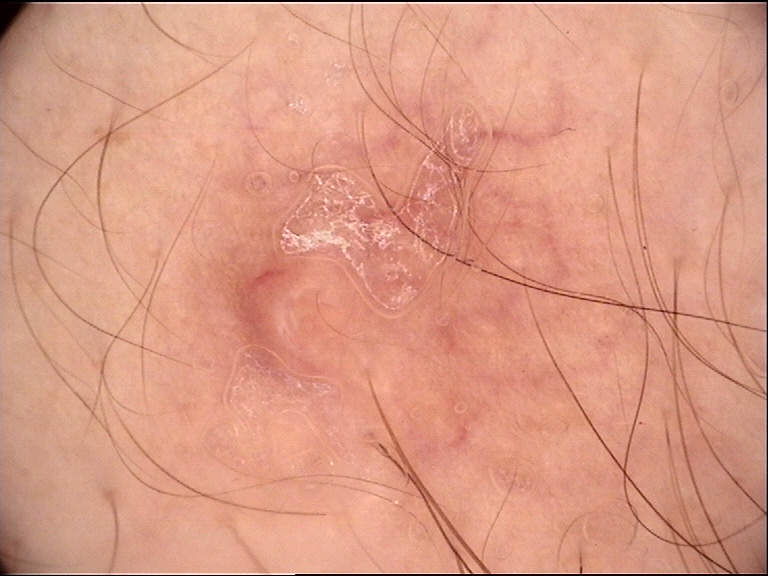Q: What kind of image is this?
A: dermoscopy
Q: What is the lesion category?
A: banal
Q: What was the diagnostic impression?
A: dermal nevus (expert consensus)